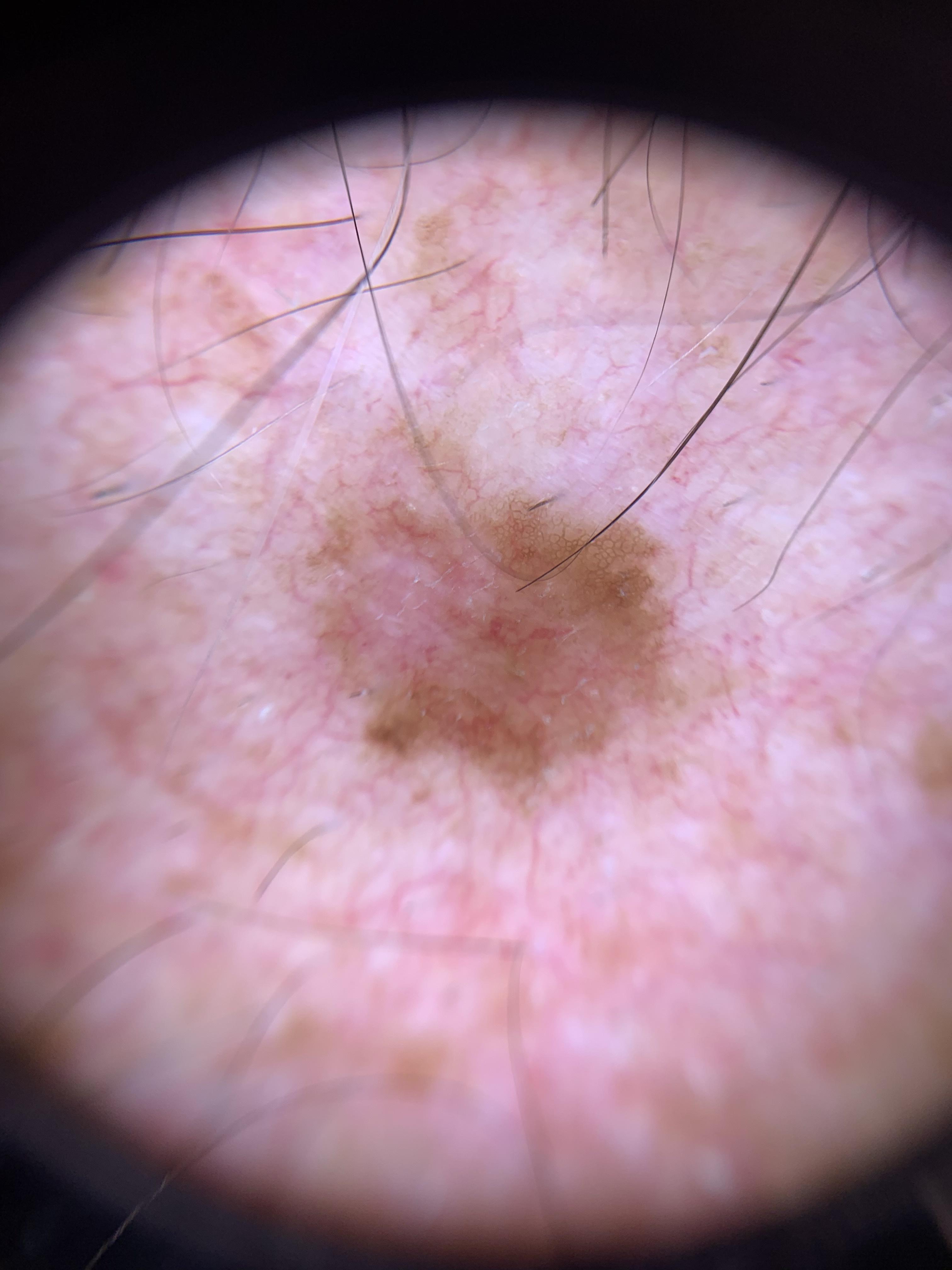A skin lesion imaged with a dermatoscope.
Fitzpatrick phototype II.
The lesion is located on the anterior trunk.
Biopsy-confirmed as a malignant, adnexal lesion — a basal cell carcinoma.